A dermoscopic close-up of a skin lesion:
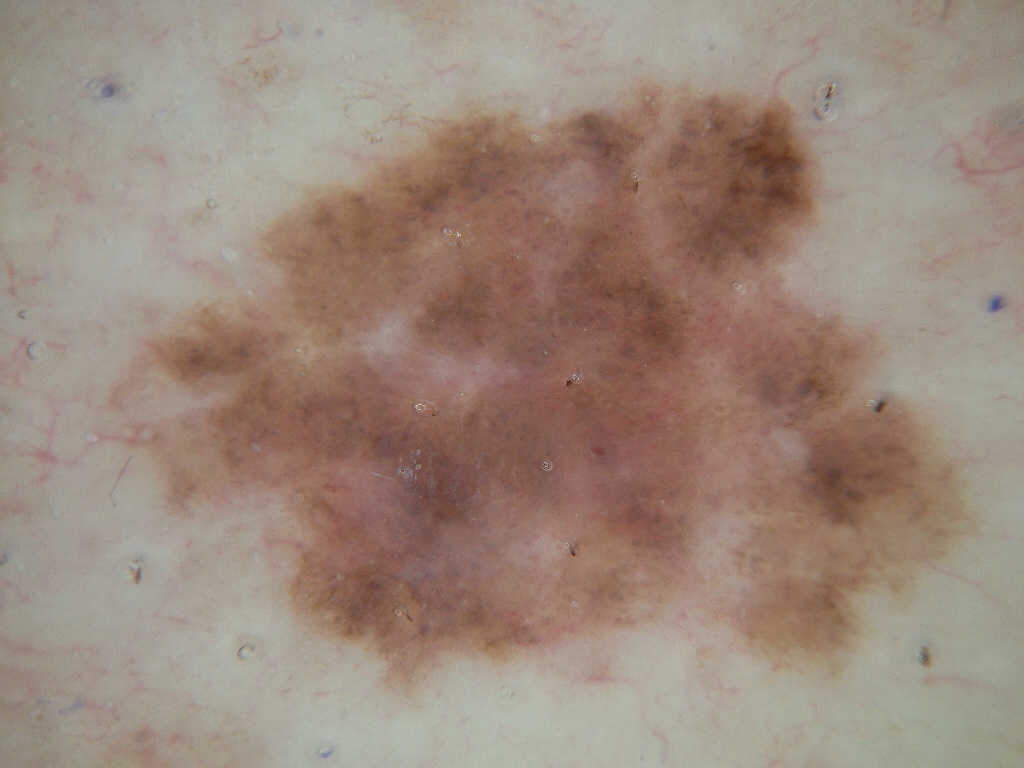<lesion>
  <dermoscopic_features>
    <present/>
    <absent>milia-like cysts, streaks, pigment network, negative network, globules</absent>
  </dermoscopic_features>
  <lesion_location>
    <bbox_xyxy>98, 75, 980, 685</bbox_xyxy>
  </lesion_location>
  <diagnosis>
    <name>melanoma</name>
    <malignancy>malignant</malignancy>
    <lineage>melanocytic</lineage>
    <provenance>histopathology</provenance>
  </diagnosis>
</lesion>